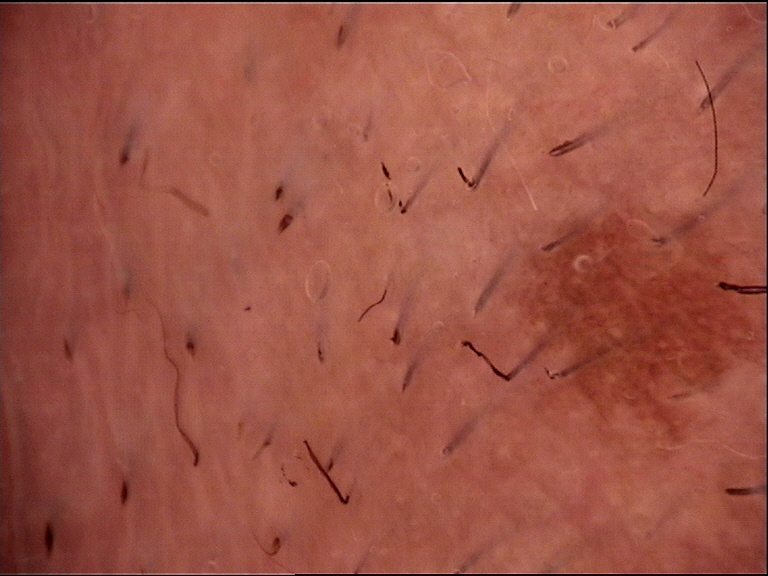Conclusion: Labeled as a benign lesion — a lentigo simplex.